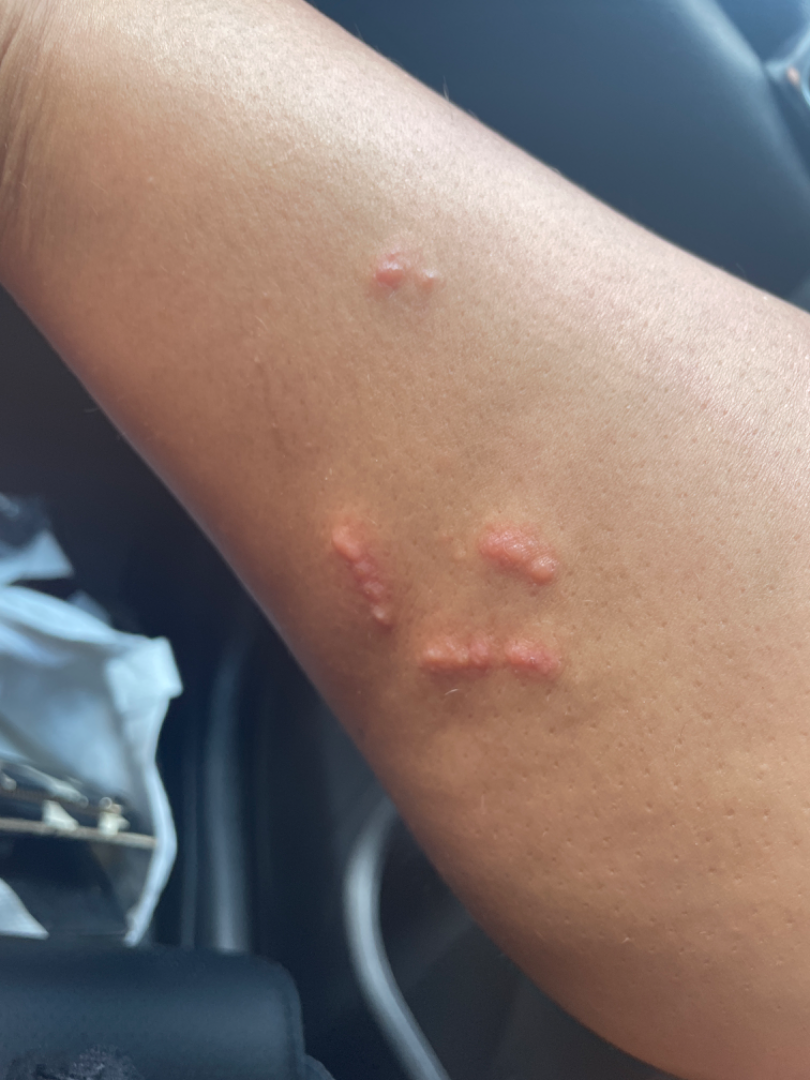Q: What is the patient's skin tone?
A: lay graders estimated MST 3 or 4 (two reviewer pools)
Q: Duration?
A: less than one week
Q: What is the affected area?
A: palm, leg and back of the hand
Q: Reported symptoms?
A: itching
Q: Texture?
A: fluid-filled and raised or bumpy
Q: How does the patient describe it?
A: a rash
Q: What is the framing?
A: close-up
Q: What conditions are considered?
A: Insect Bite (considered); Allergic Contact Dermatitis (considered)